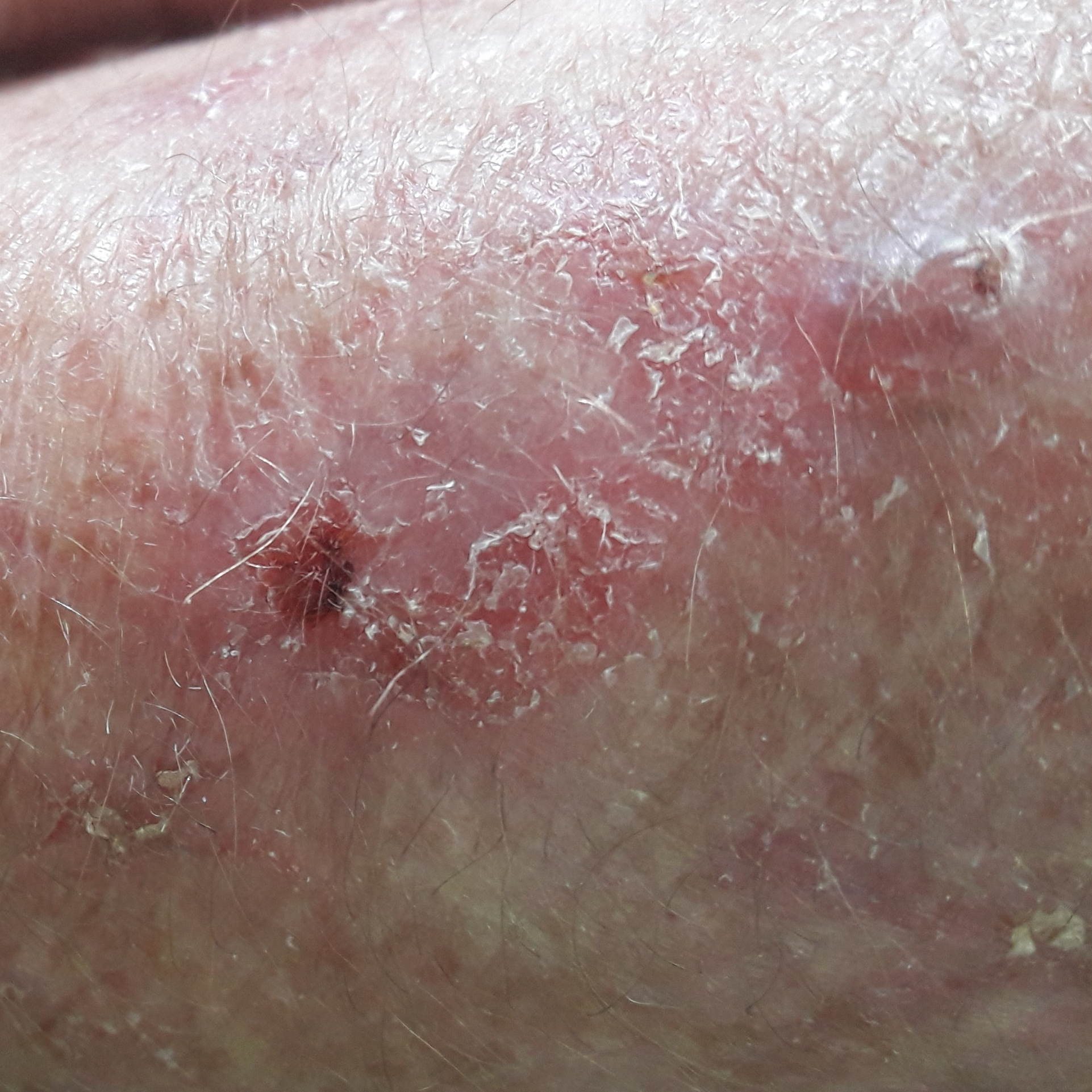size: 6x5 mm
patient-reported symptoms: itching, growth, elevation / no change in appearance, no pain
impression: actinic keratosis (clinical consensus)